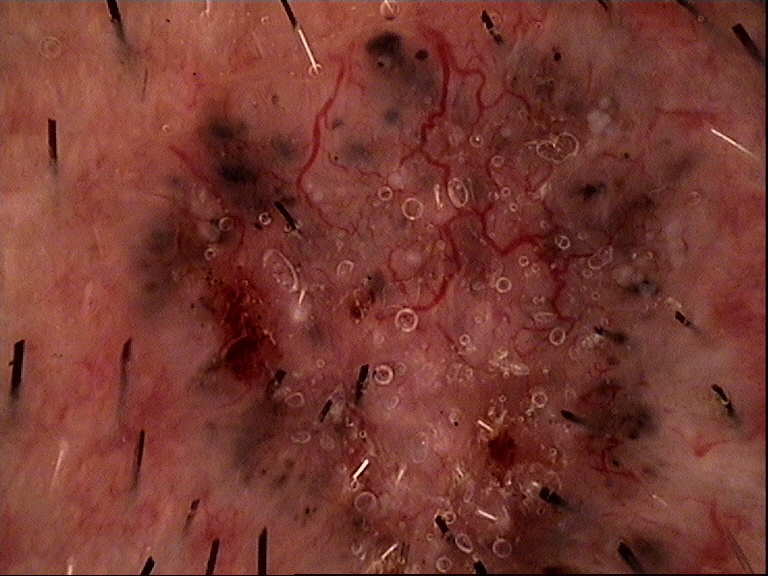Case:
A dermoscopy image of a single skin lesion.
Pathology:
The biopsy diagnosis was a basal cell carcinoma.